A clinical photo of a skin lesion taken with a smartphone — 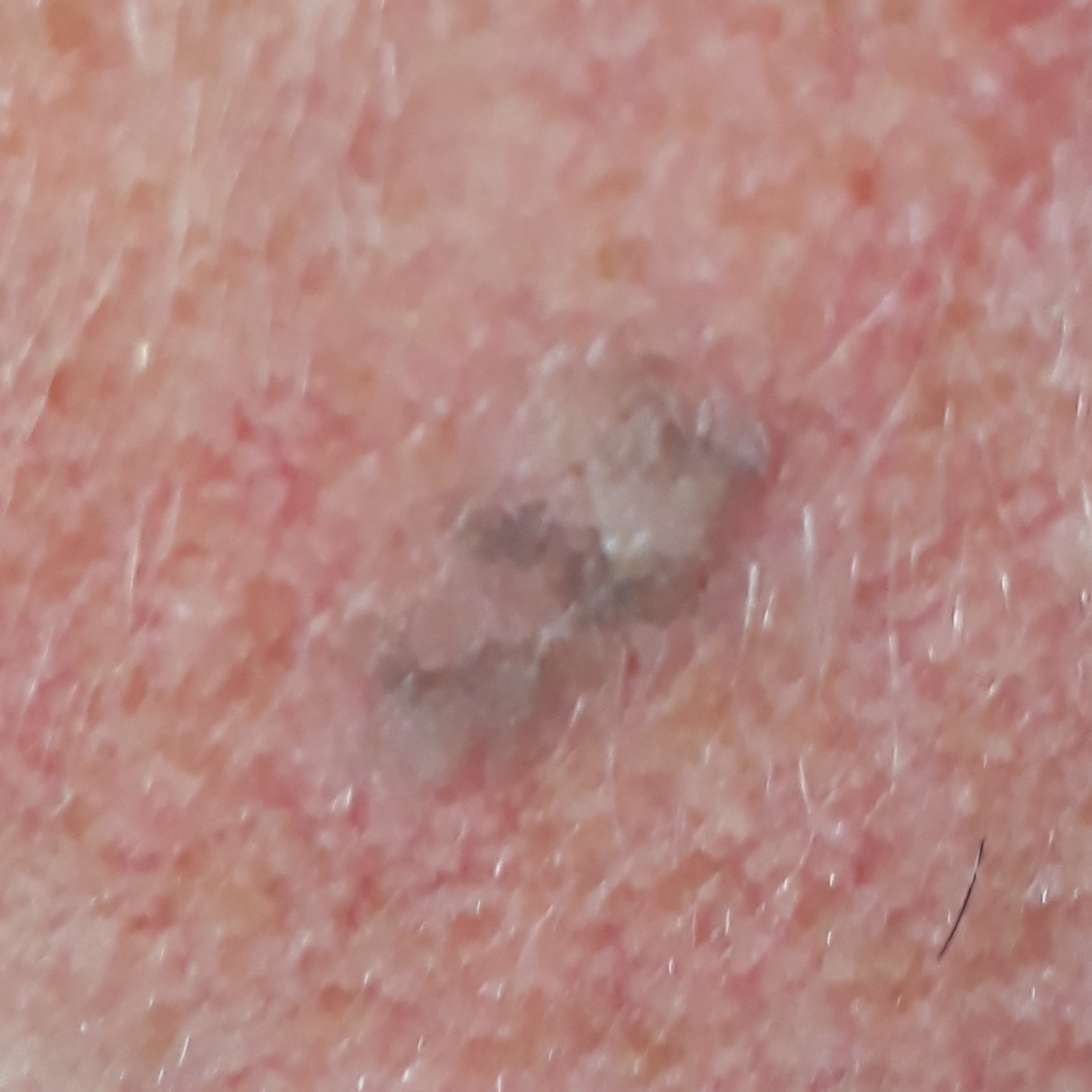location = the face; patient-reported symptoms = elevation / no change in appearance, no growth; diagnostic label = seborrheic keratosis (clinical consensus).